The patient is 40–49, female; close-up view:
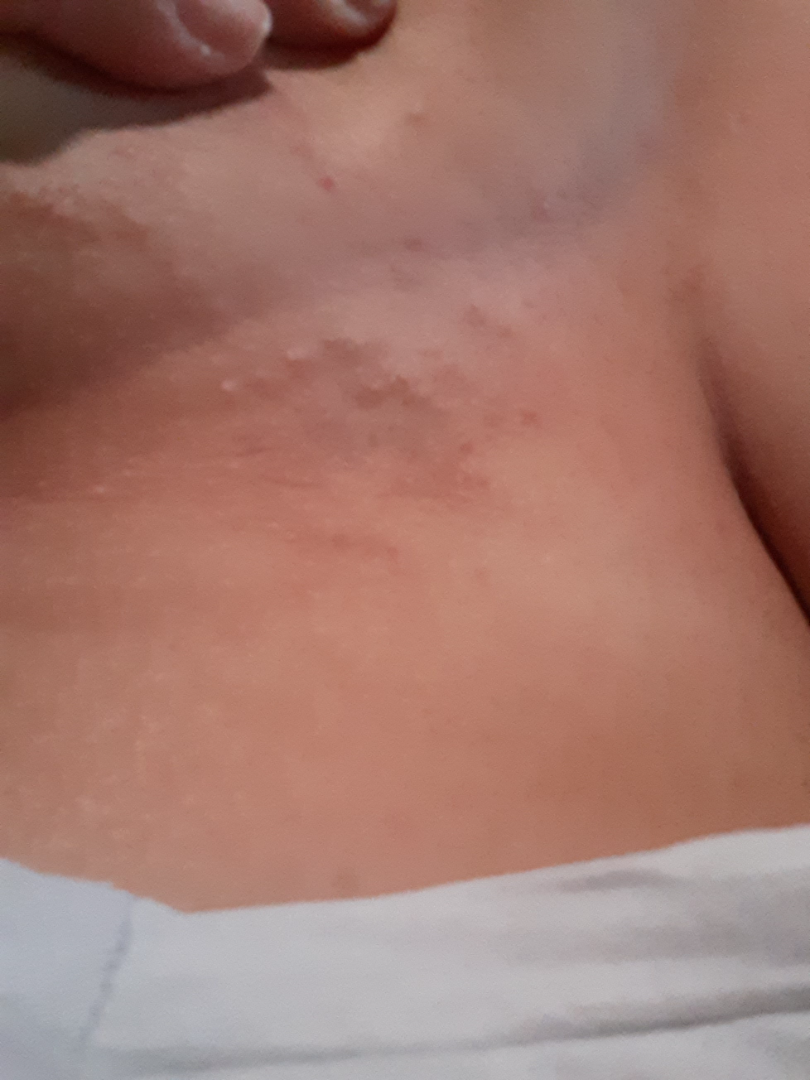assessment: consistent with Eczema.